The photograph was taken at a distance · the subject is 30–39, female:
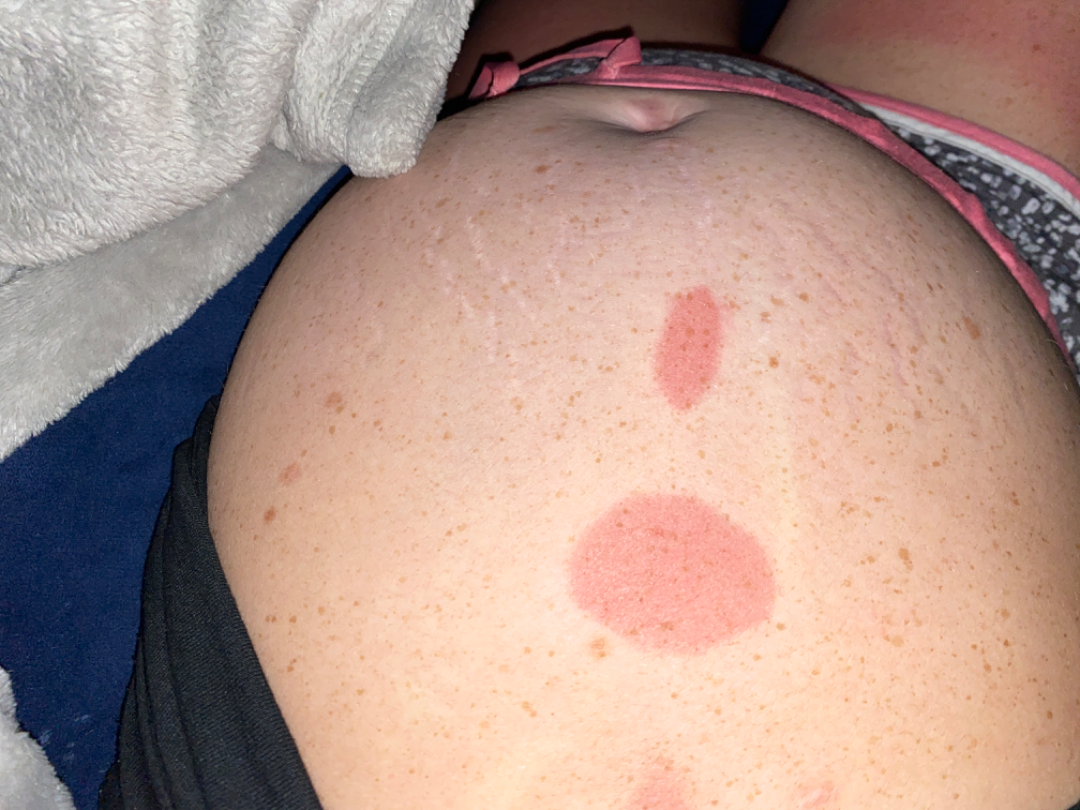assessment=not assessable | lesion texture=flat.